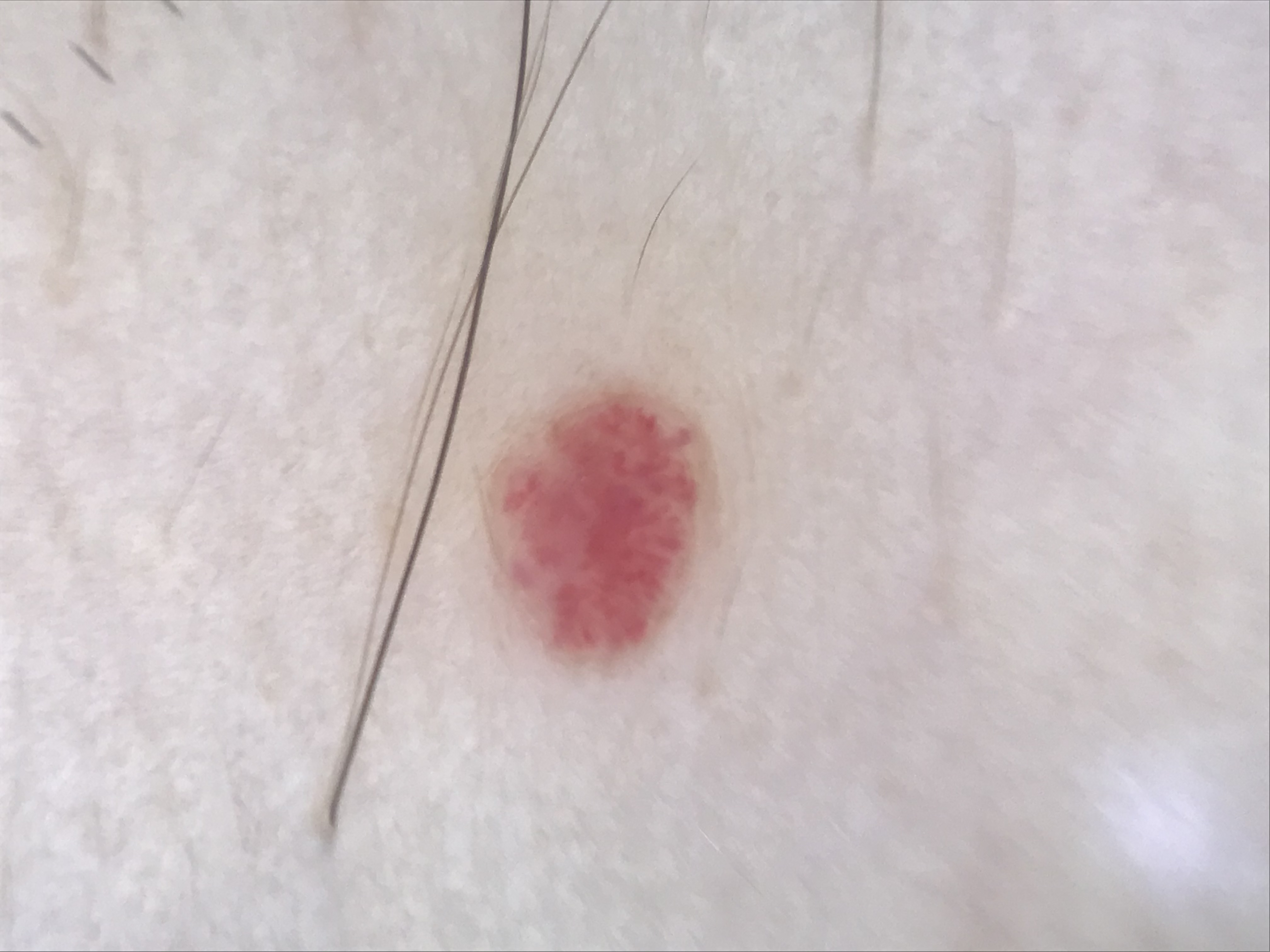Case:
* modality · dermatoscopy
* diagnosis · hemangioma (expert consensus)